The contributor is a male aged 40–49. The lesion is described as raised or bumpy and fluid-filled. The patient also reports shortness of breath. Present for less than one week. The palm is involved. Reported lesion symptoms include burning and bothersome appearance. The photo was captured at a distance. The patient described the issue as a rash:
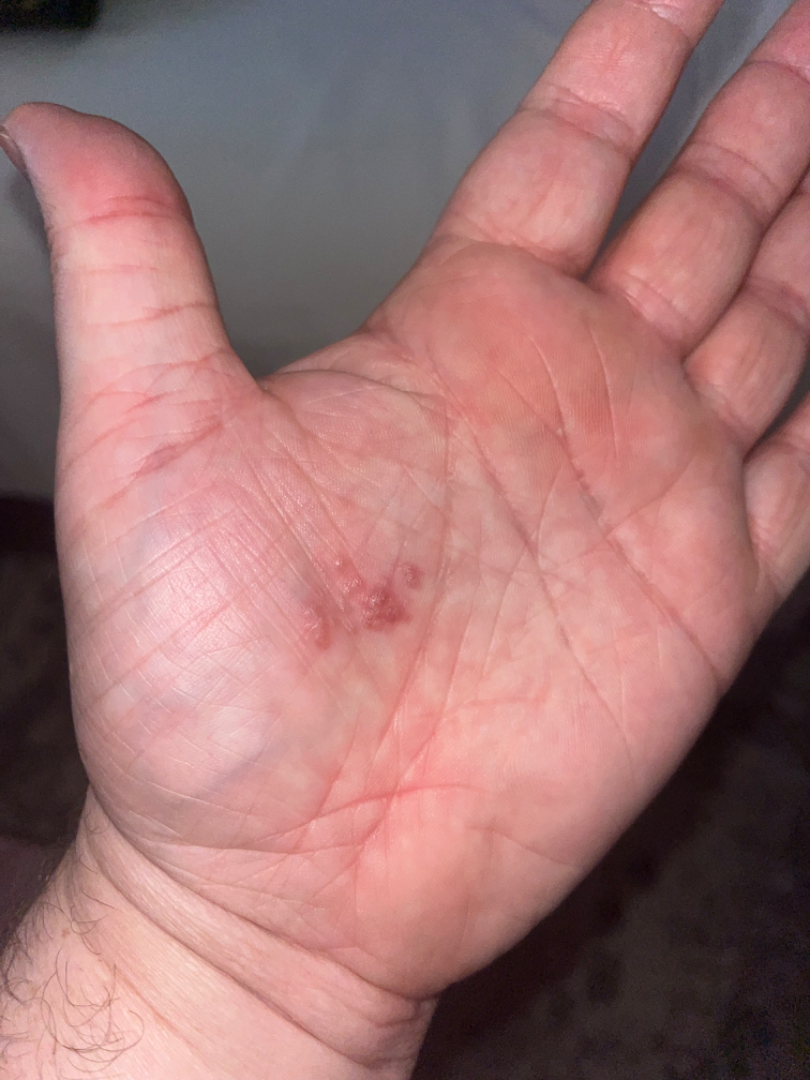{"differential": {"leading": ["Eczema"]}}